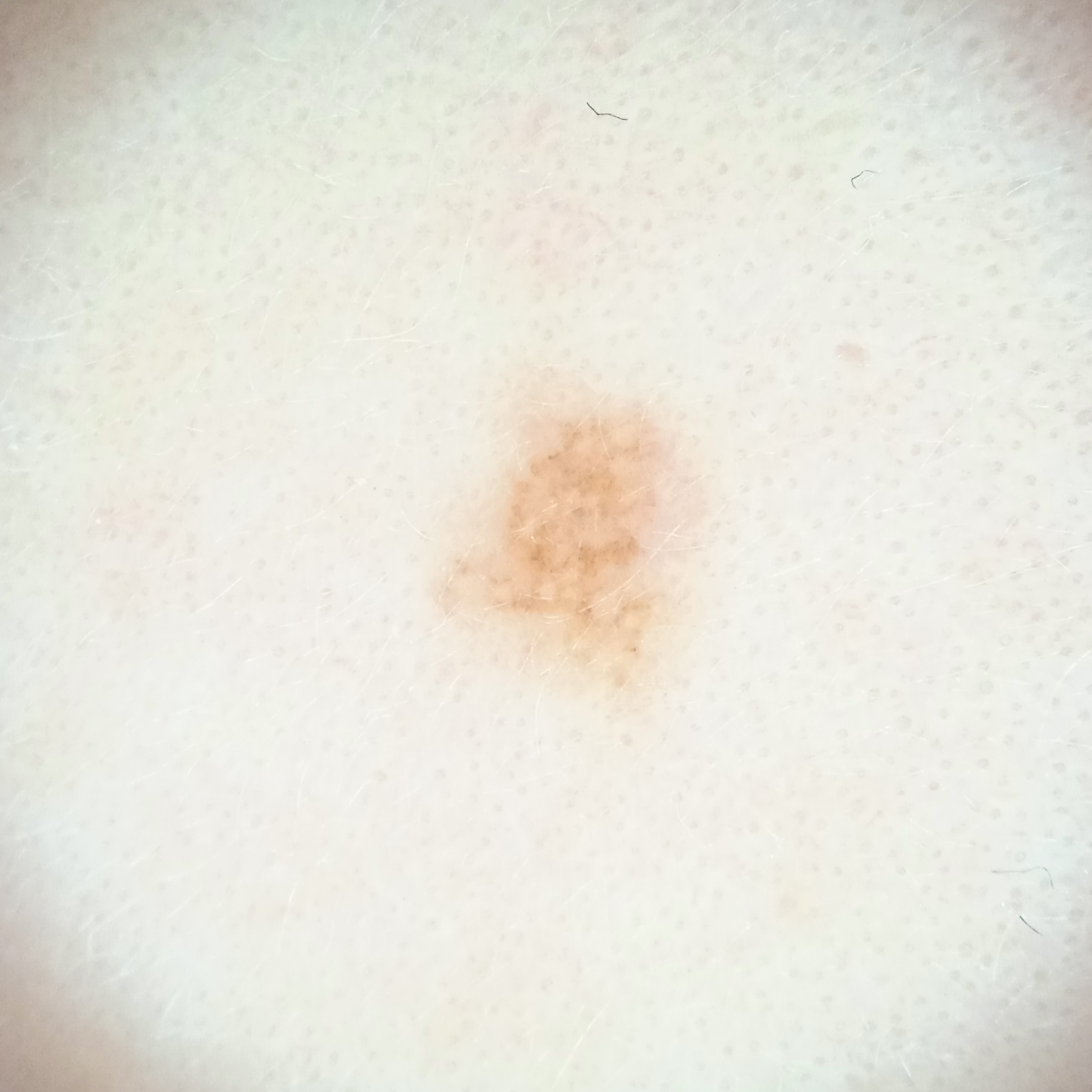A dermoscopic image of a skin lesion. The patient says their skin reddens with sun exposure. A female subject 15 years of age. Imaged for a research study, with no referral diagnosis recorded. The patient describes having few moles overall. The lesion is on the face. Measuring roughly 3.2 mm. The lesion was assessed as a melanocytic nevus.